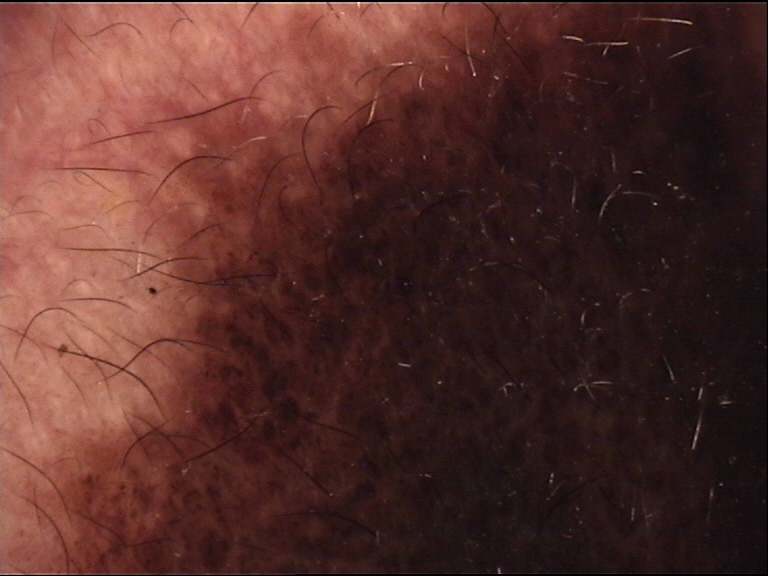Case:
The architecture is that of a banal lesion.
Impression:
Consistent with a congenital compound nevus.